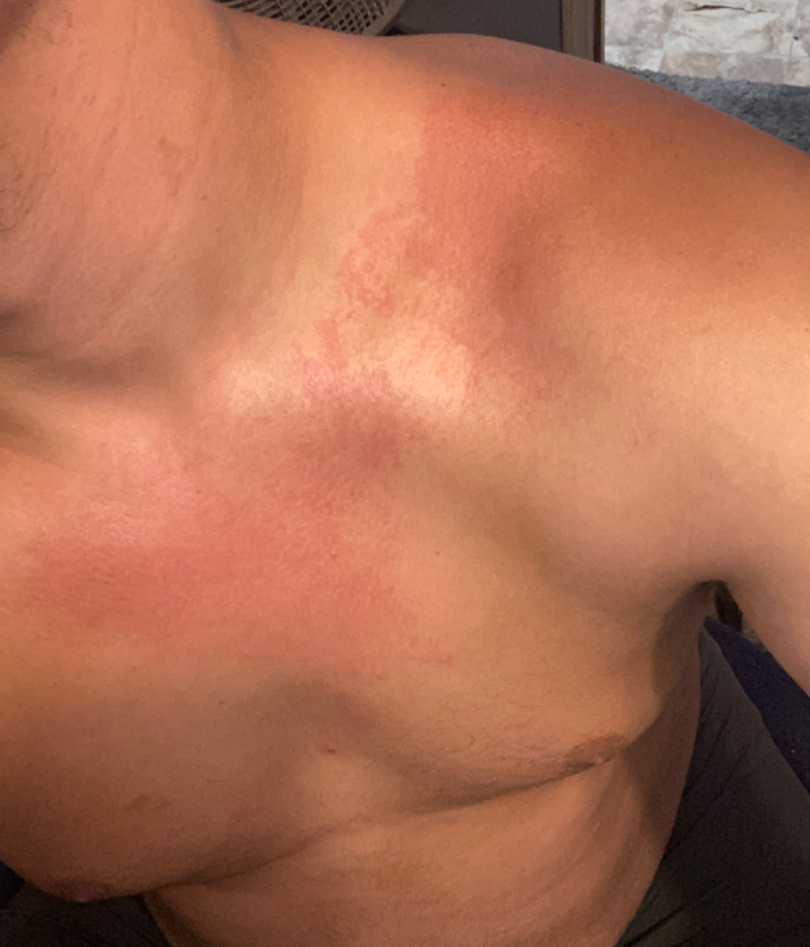The skin findings could not be characterized from the image. The lesion is associated with itching and burning. The subject is a male aged 18–29. The patient considered this a rash. Present for about one day. The lesion is described as flat. The front of the torso is involved. The photograph was taken at an angle.